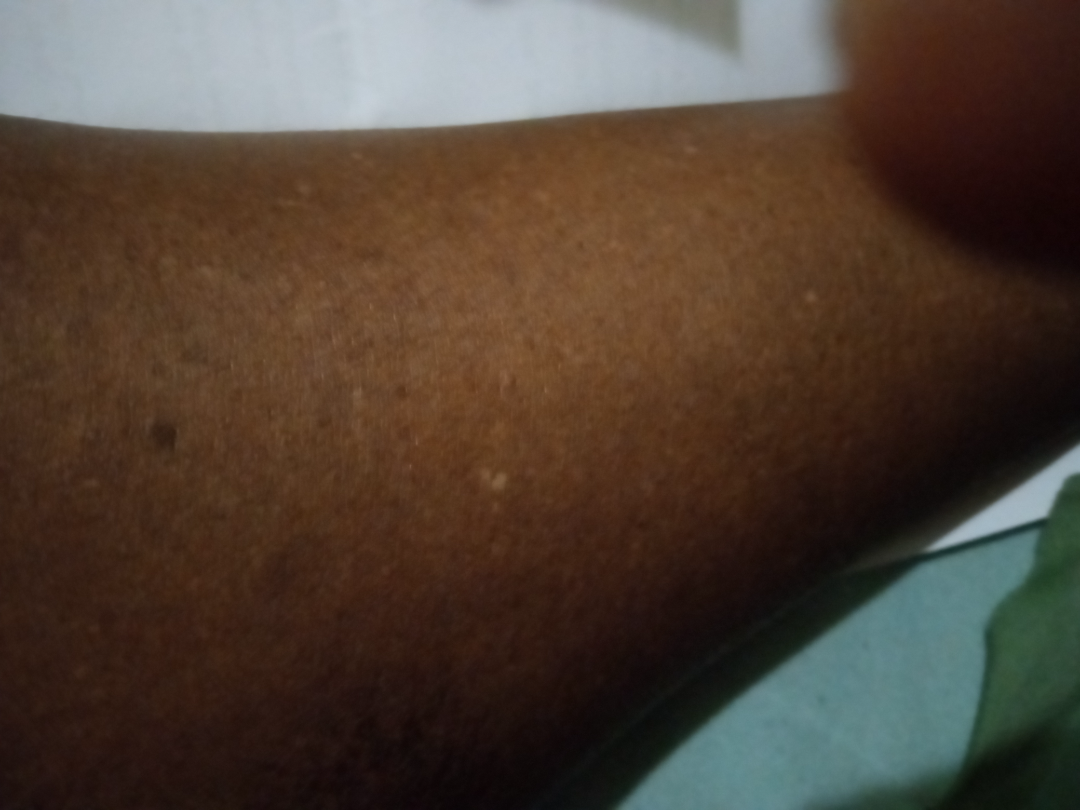No discernible pathology was noted by the reviewing dermatologist.